A dermoscopic close-up of a skin lesion:
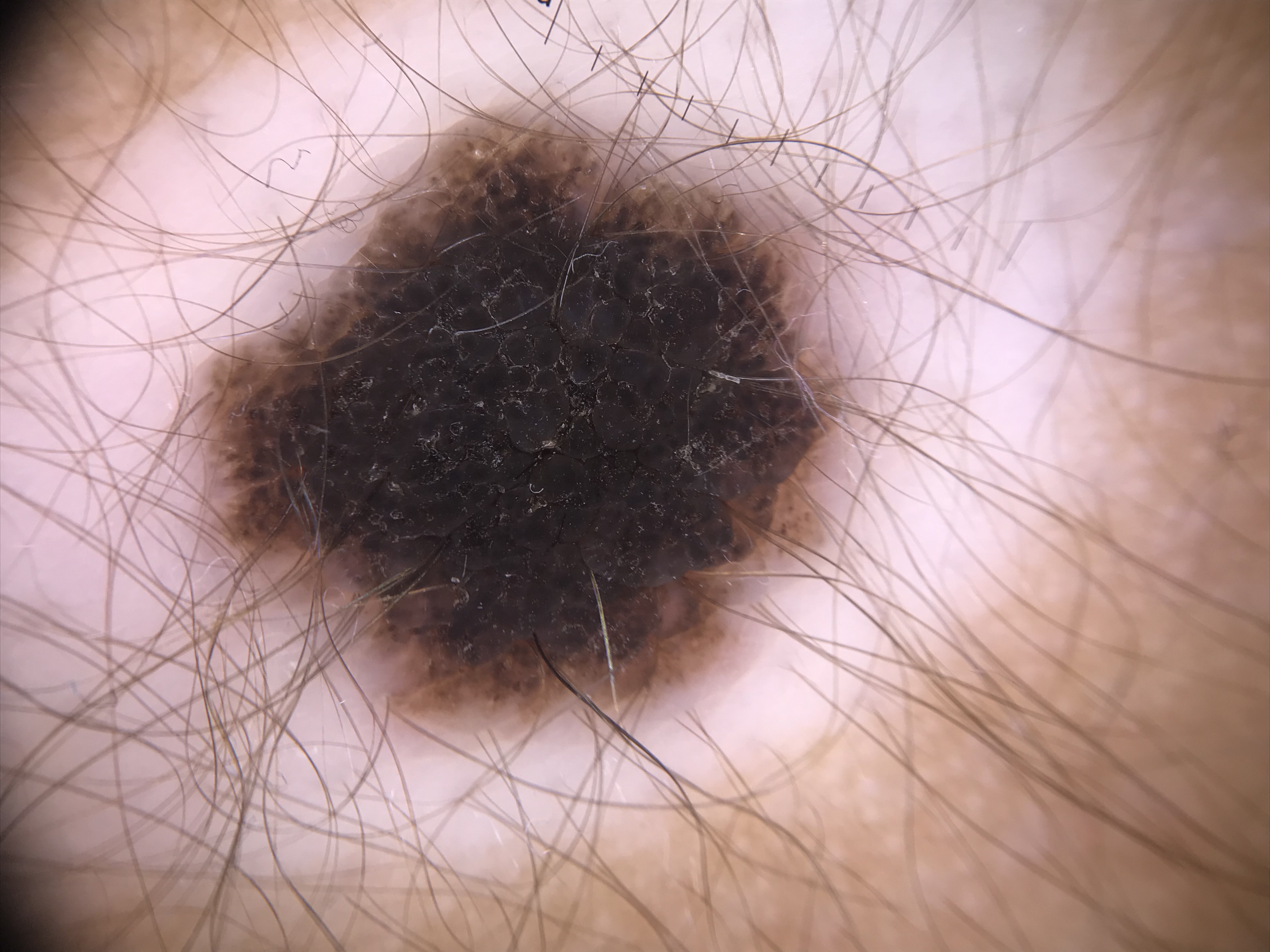  lesion_type:
    main_class: banal
    pattern: compound
  diagnosis:
    name: congenital compound nevus
    code: ccb
    malignancy: benign
    super_class: melanocytic
    confirmation: expert consensus